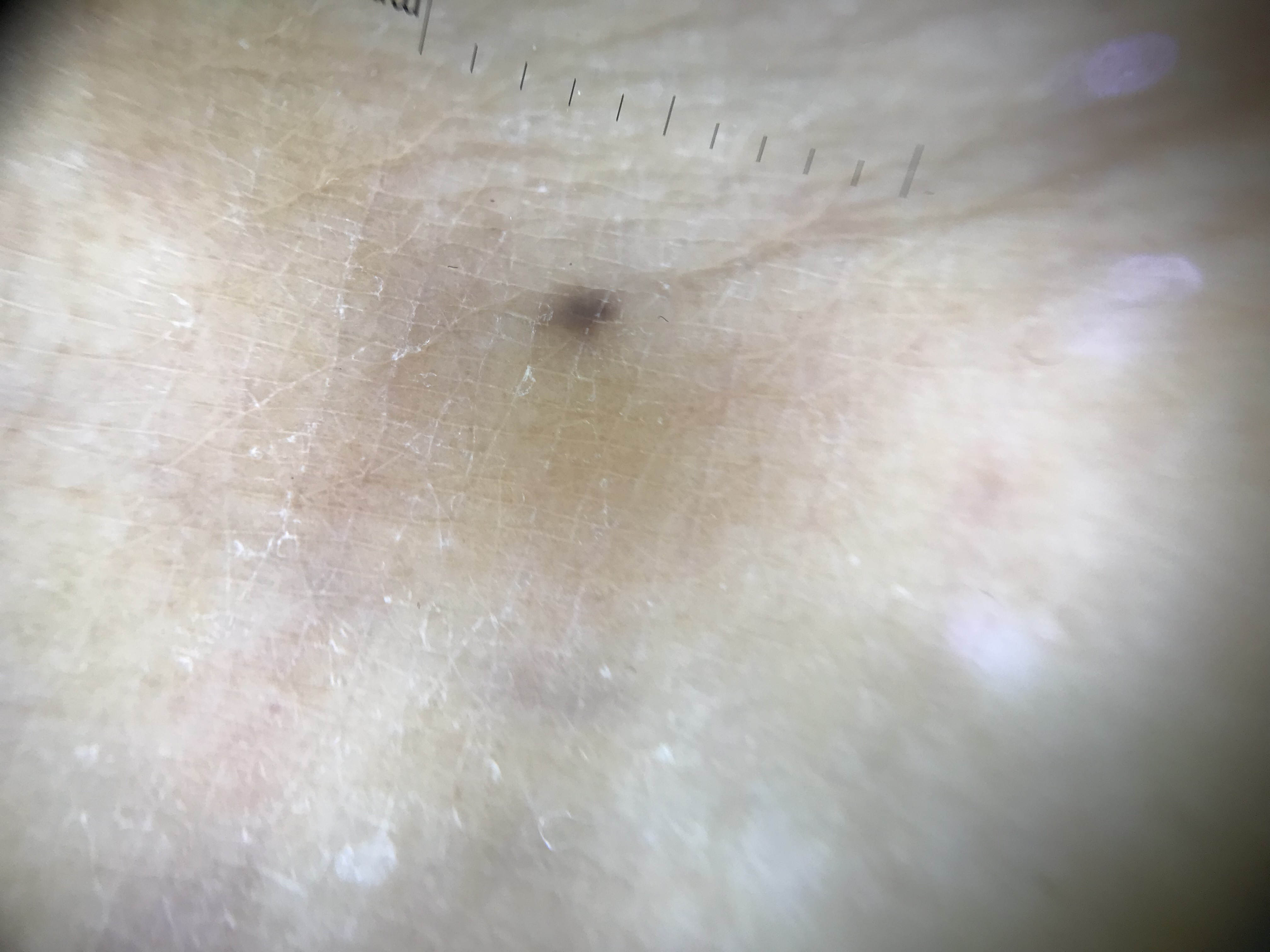<case>
  <diagnosis>
    <name>acral junctional nevus</name>
    <code>ajb</code>
    <malignancy>benign</malignancy>
    <super_class>melanocytic</super_class>
    <confirmation>expert consensus</confirmation>
  </diagnosis>
</case>